A dermoscopic close-up of a skin lesion · per the chart, a prior melanoma · the patient was assessed as Fitzpatrick phototype II · a female patient aged approximately 60: 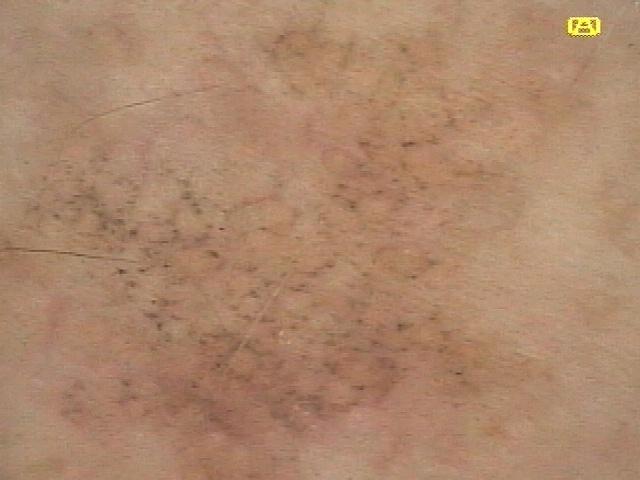The lesion is located on the head or neck.
Histopathological examination showed a benign, epidermal lesion — a solar lentigo.